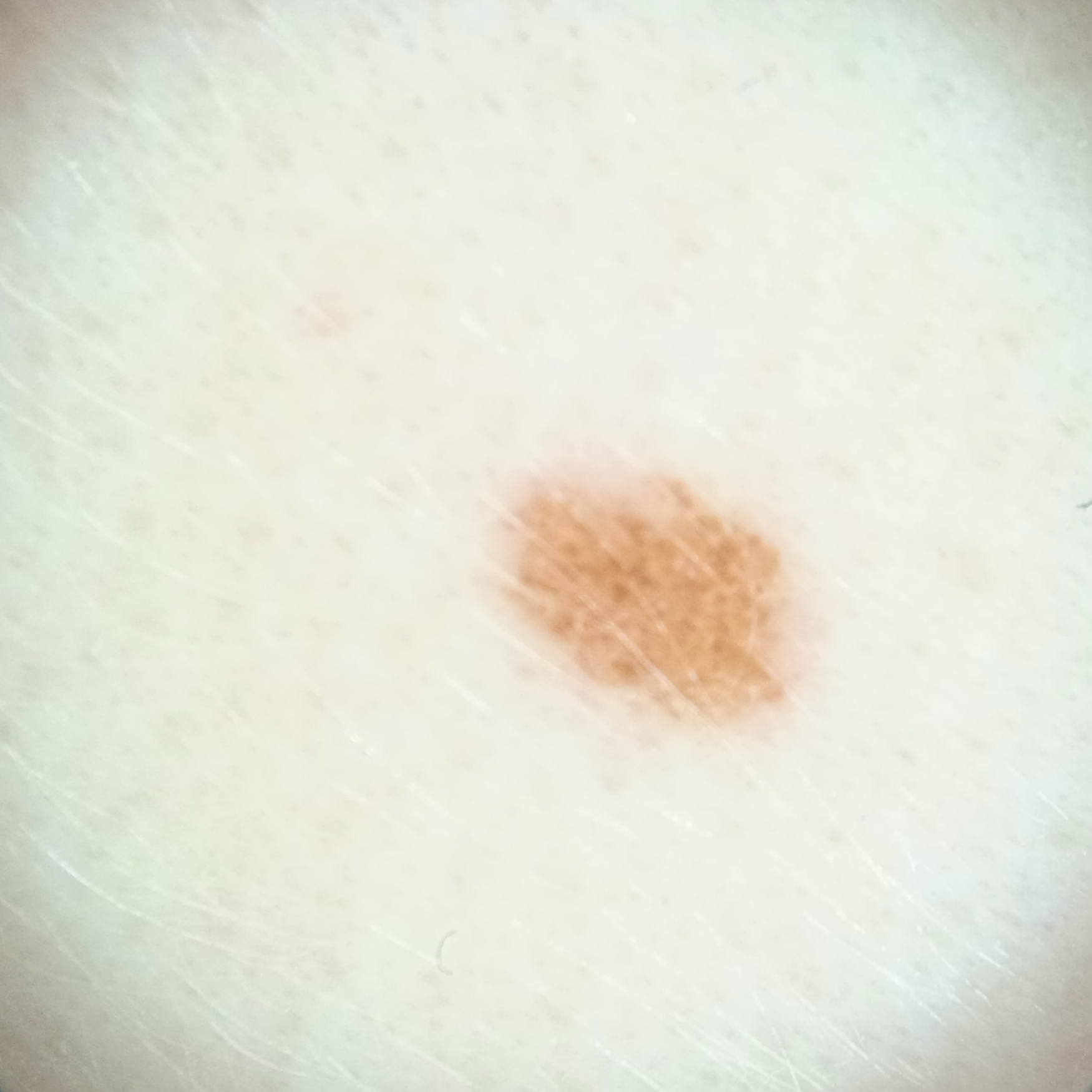<case>
  <diagnosis>
    <name>melanocytic nevus</name>
    <malignancy>benign</malignancy>
  </diagnosis>
</case>